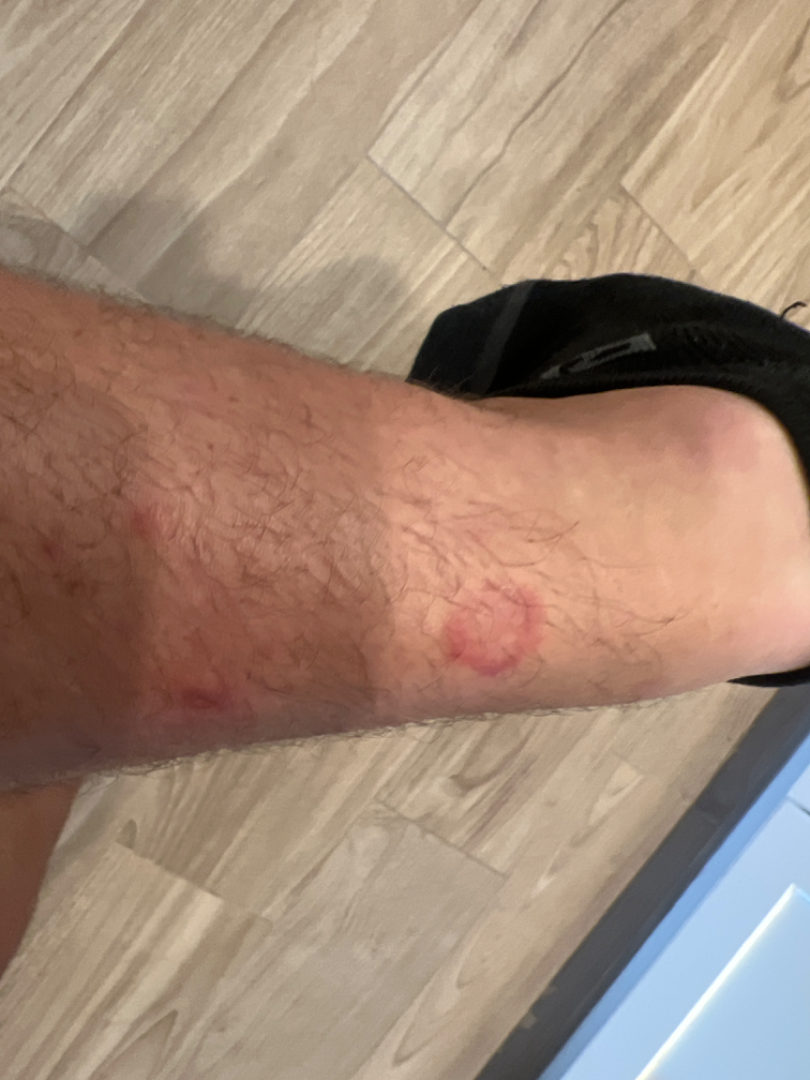Review:
No differential diagnosis could be assigned on photographic review.
Patient information:
The photograph is a close-up of the affected area. The patient is a male aged 18–29. The lesion involves the leg.